A dermoscopic close-up of a skin lesion.
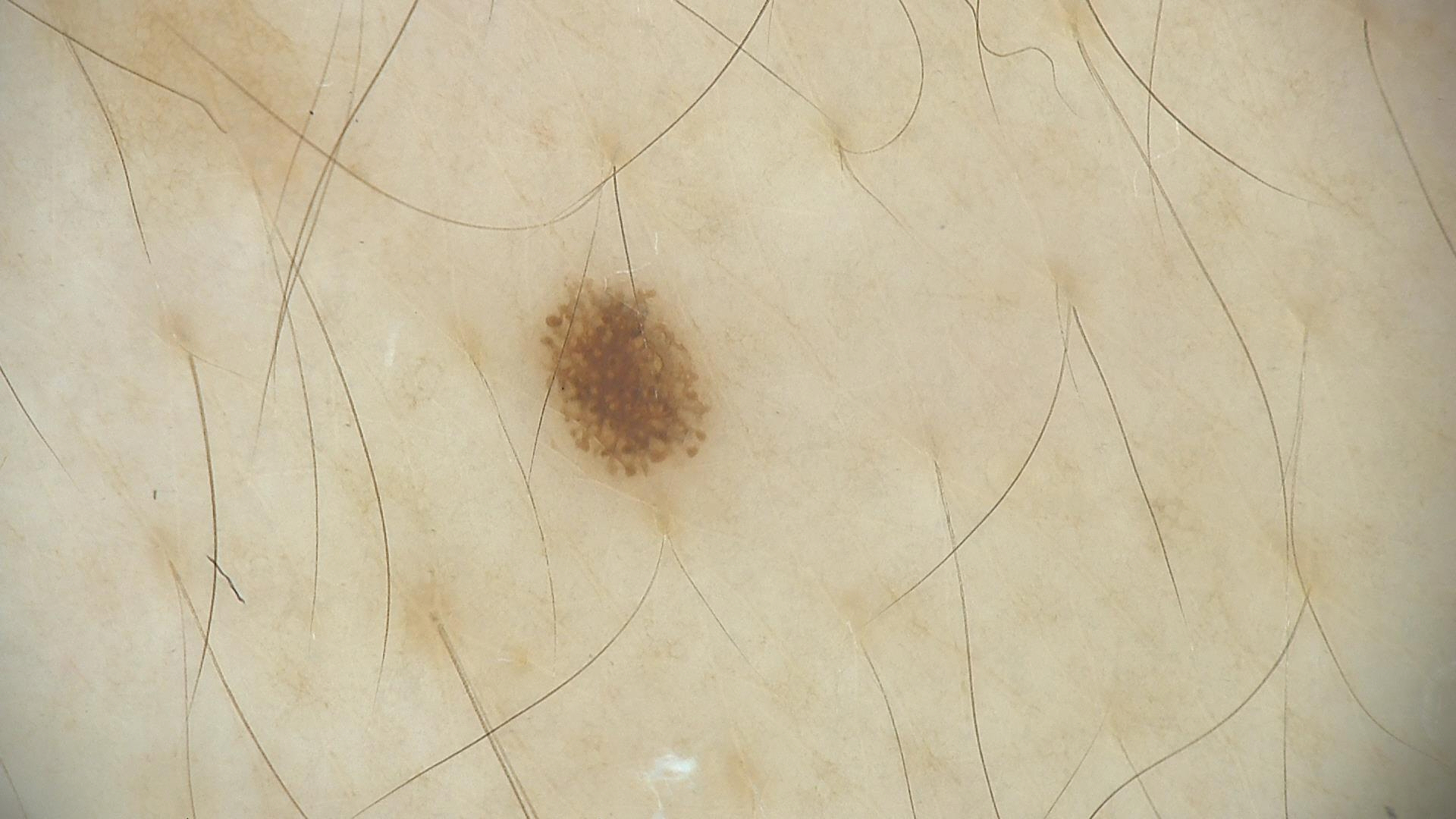diagnostic label = dysplastic junctional nevus (expert consensus).